The affected area is the arm. The photo was captured at an angle. The patient considered this a rash. Texture is reported as raised or bumpy and rough or flaky. The lesion is associated with enlargement, burning, bothersome appearance and itching — 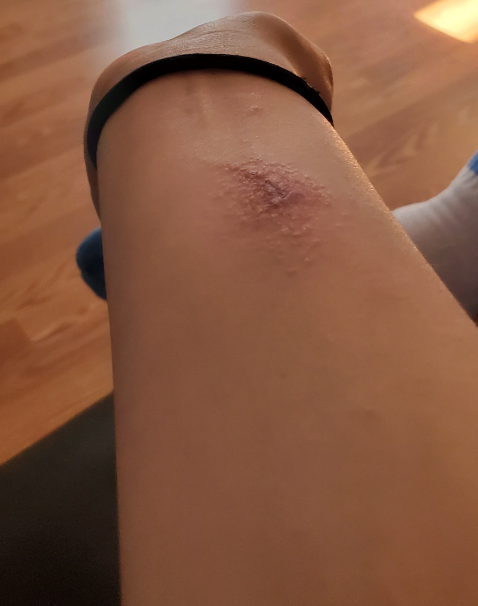Q: What conditions are considered?
A: Impetigo and Allergic Contact Dermatitis were considered with similar weight